A male patient in their mid-60s; by history, prior skin cancer (patient or family), tobacco use, pesticide exposure, and prior malignancy (patient or family):
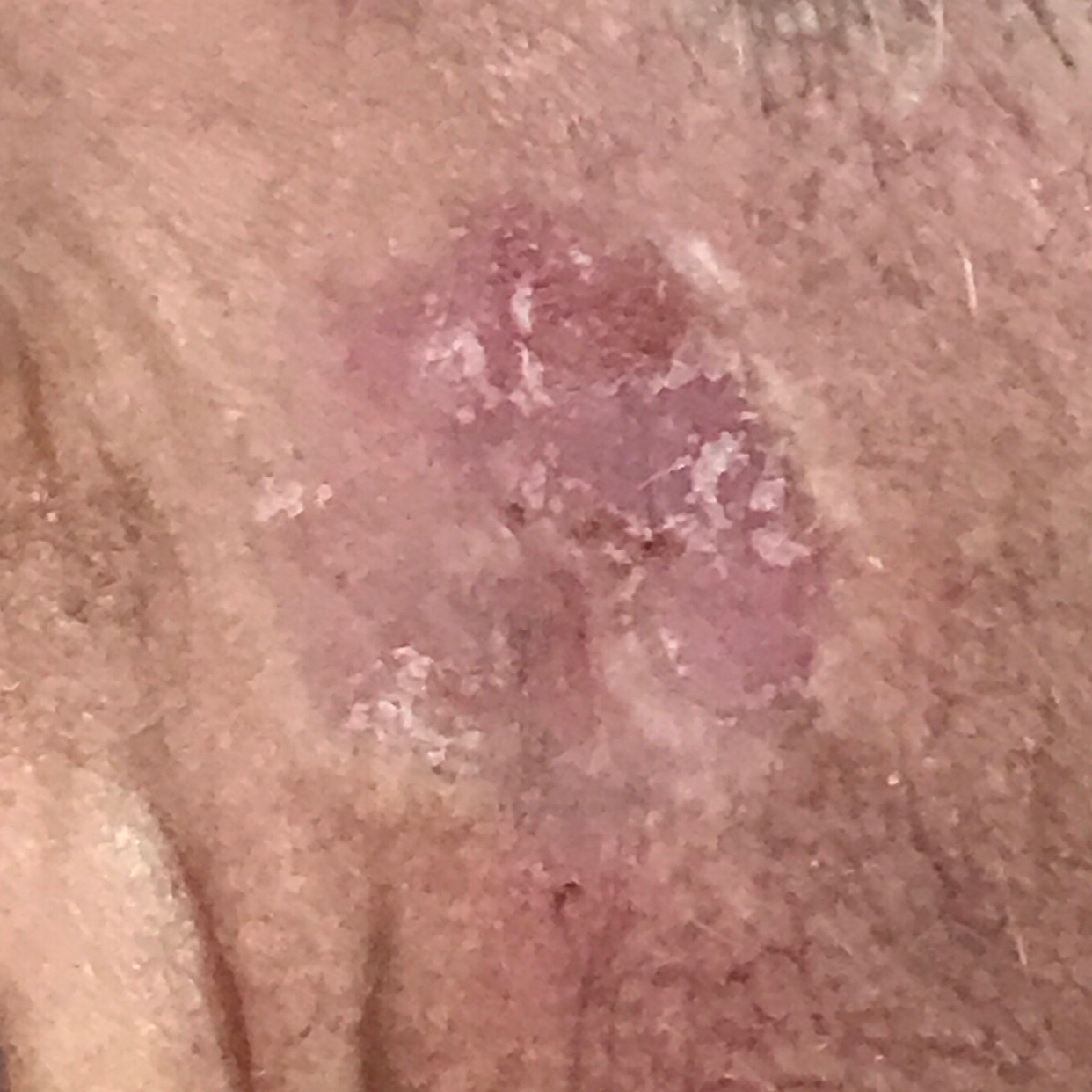The lesion is roughly 11 by 8 mm.
The patient reports that the lesion itches.
Biopsy-confirmed as a malignancy — a basal cell carcinoma.